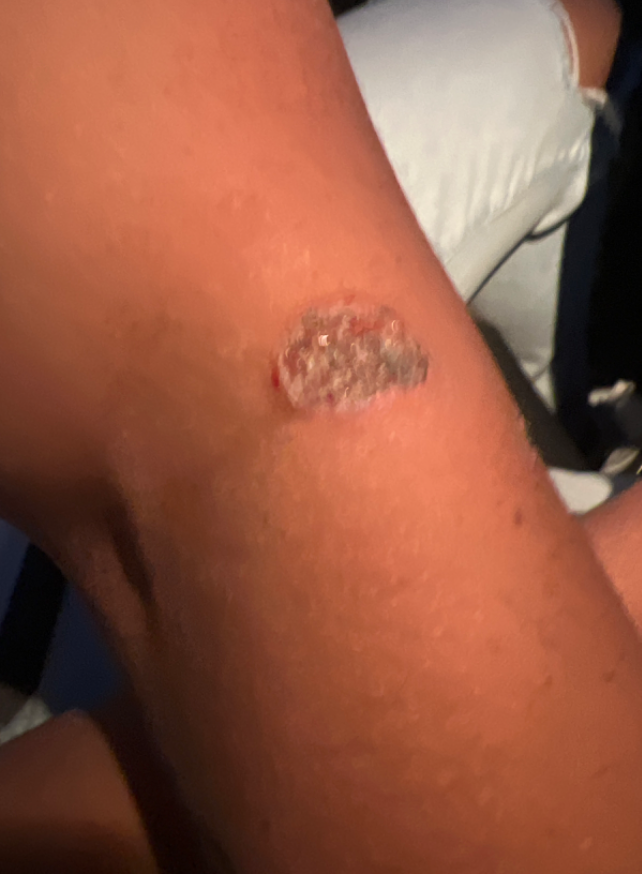Patient information: The contributor is a male aged 18–29. The arm is involved. The patient described the issue as a rash. Texture is reported as rough or flaky. Present for one to three months. The patient reported no systemic symptoms. Close-up view. Symptoms reported: bleeding, enlargement, pain, bothersome appearance, darkening and itching. Review: Three independent reviewers: the differential includes Ecthyma, Fungal dermatitis and Cutaneous leishmaniasis, with no clear leading consideration.